An image taken at an angle, texture is reported as raised or bumpy, the condition has been present for less than one week, the leg is involved, reported lesion symptoms include pain, the patient described the issue as a rash, no relevant systemic symptoms: 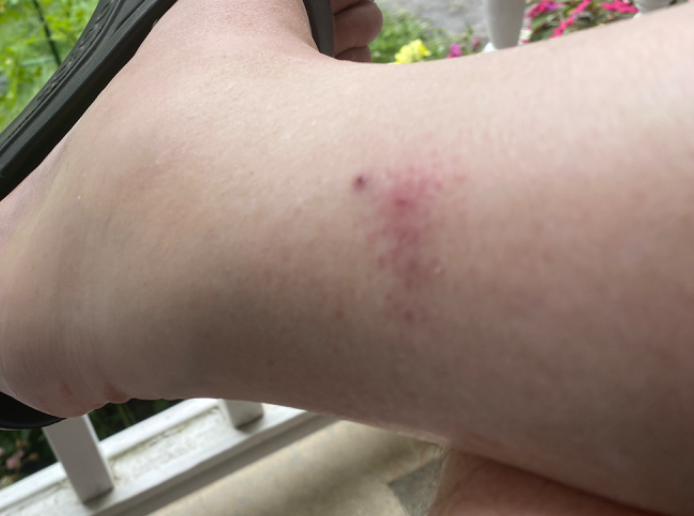Impression:
The leading consideration is Allergic Contact Dermatitis.